The contributor is 30–39, male; the photograph is a close-up of the affected area; the lesion is described as raised or bumpy; no associated lesion symptoms were reported; the affected area is the palm, front of the torso and arm; reported duration is less than one week:
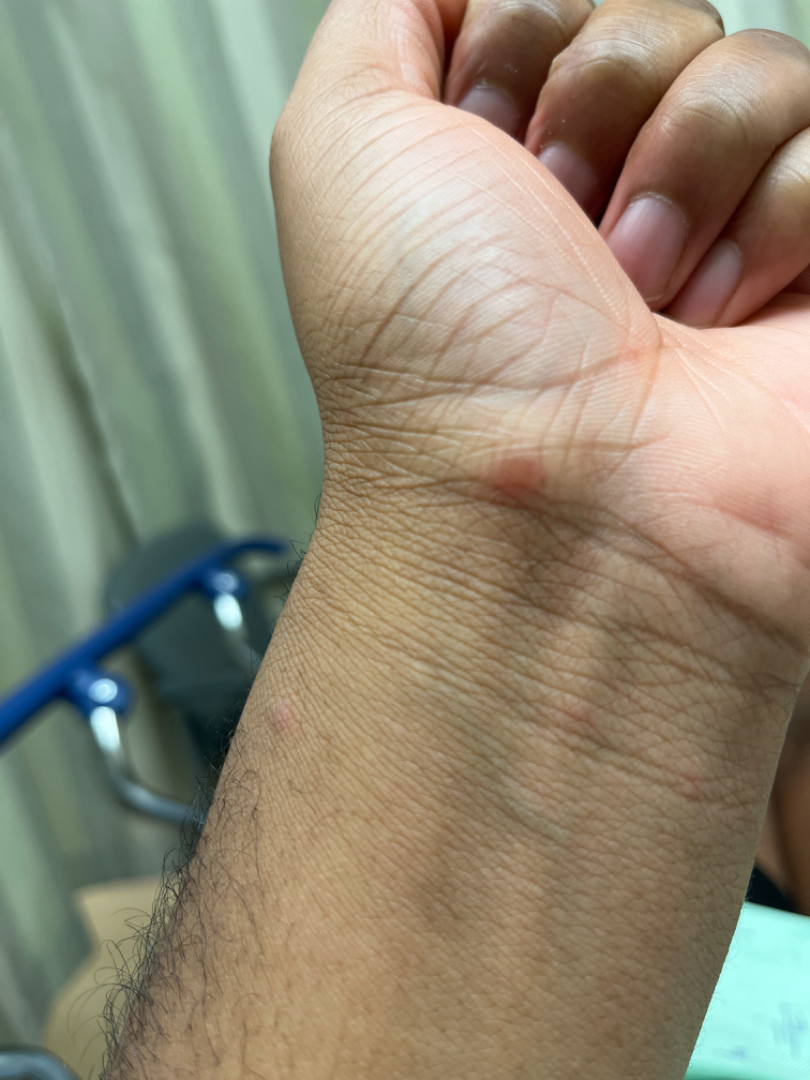Diagnostic features were not clearly distinguishable in this photograph.